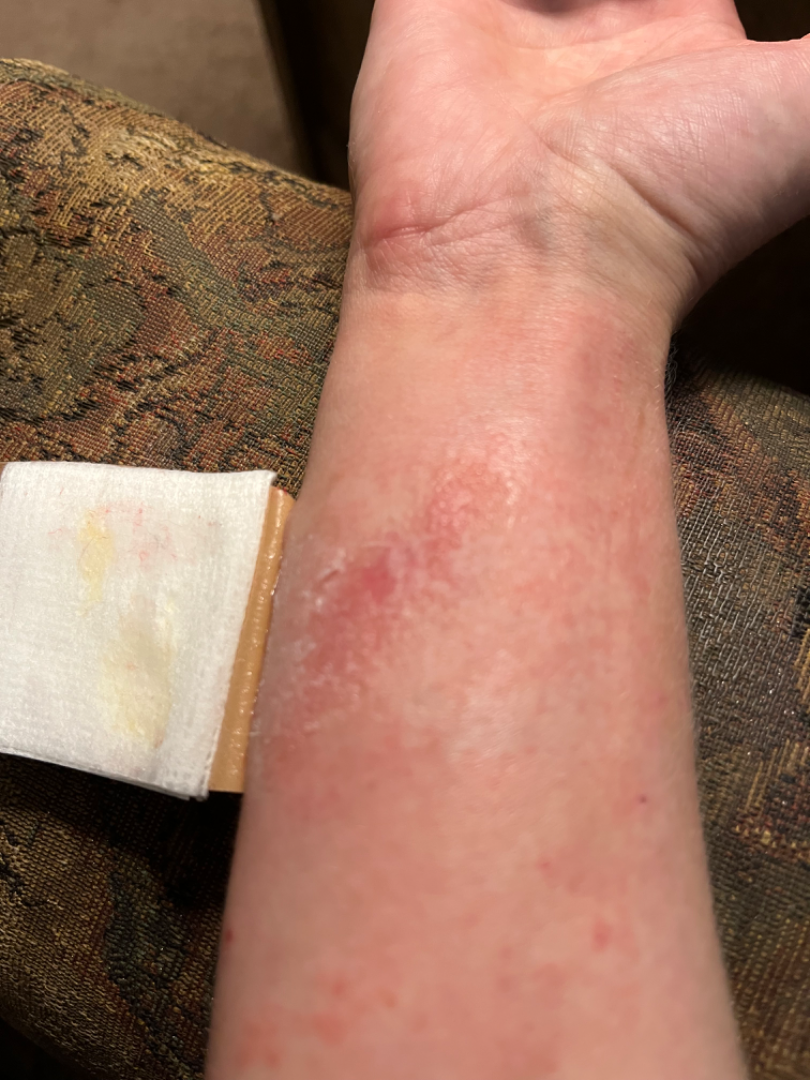Background: The photograph is a close-up of the affected area. Findings: On photographic review by a dermatologist, Eczema (41%); Allergic Contact Dermatitis (41%); Impetigo (18%).